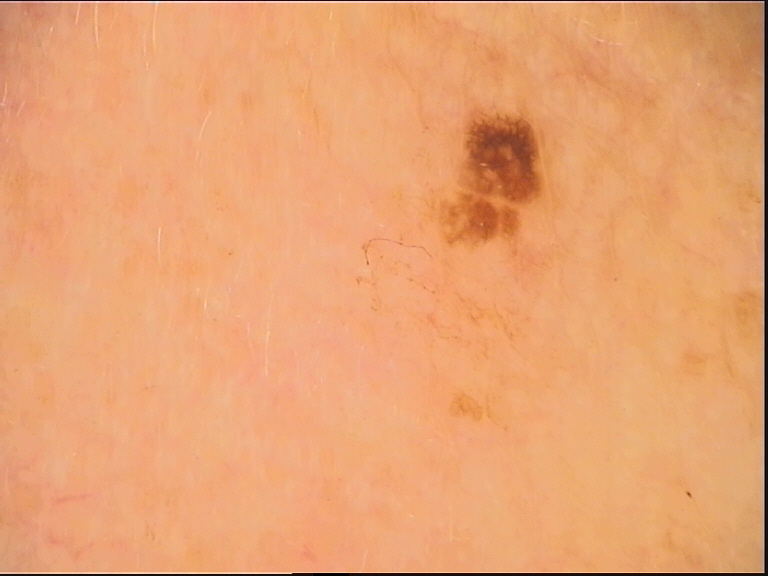modality: dermoscopy | subtype: keratinocytic | diagnosis: seborrheic keratosis (expert consensus).